The subject is 18–29, male. The lesion involves the leg. This is a close-up image — 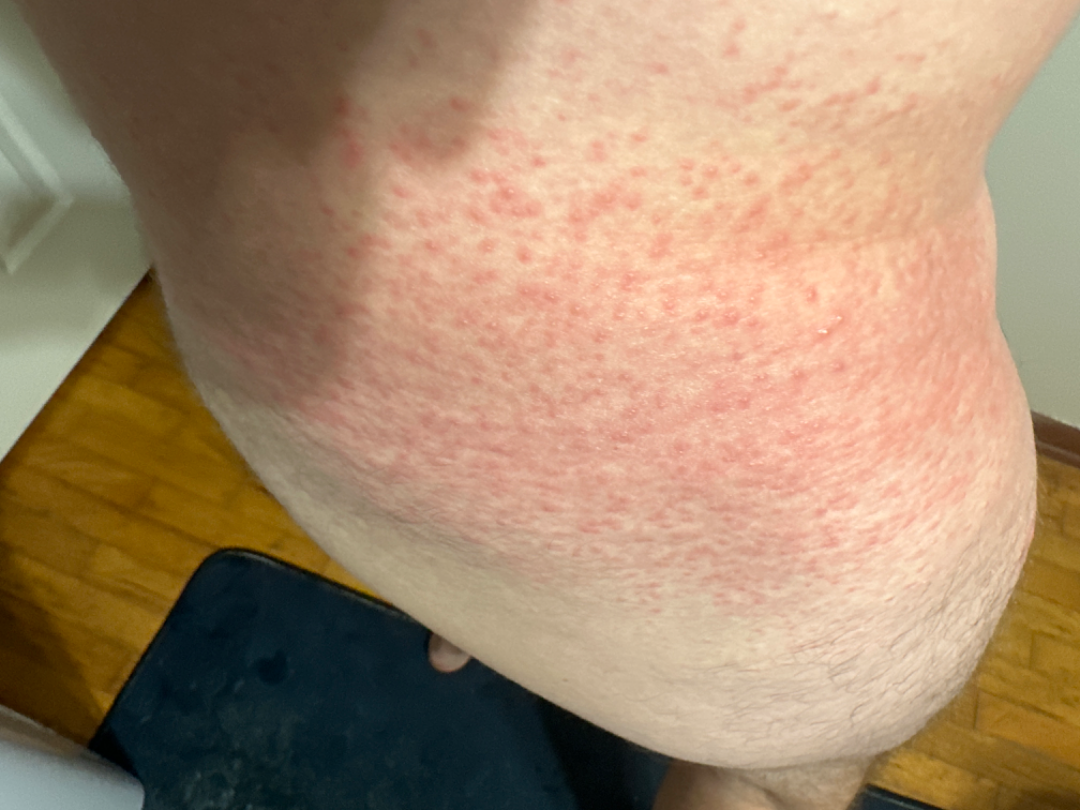| feature | finding |
|---|---|
| duration | less than one week |
| patient describes the issue as | a rash |
| lesion symptoms | bothersome appearance, itching and burning |
| skin tone | FST II |
| described texture | raised or bumpy |
| dermatologist impression | single-reviewer assessment: most consistent with Eczema; also consider Pityriasis rubra pilaris |